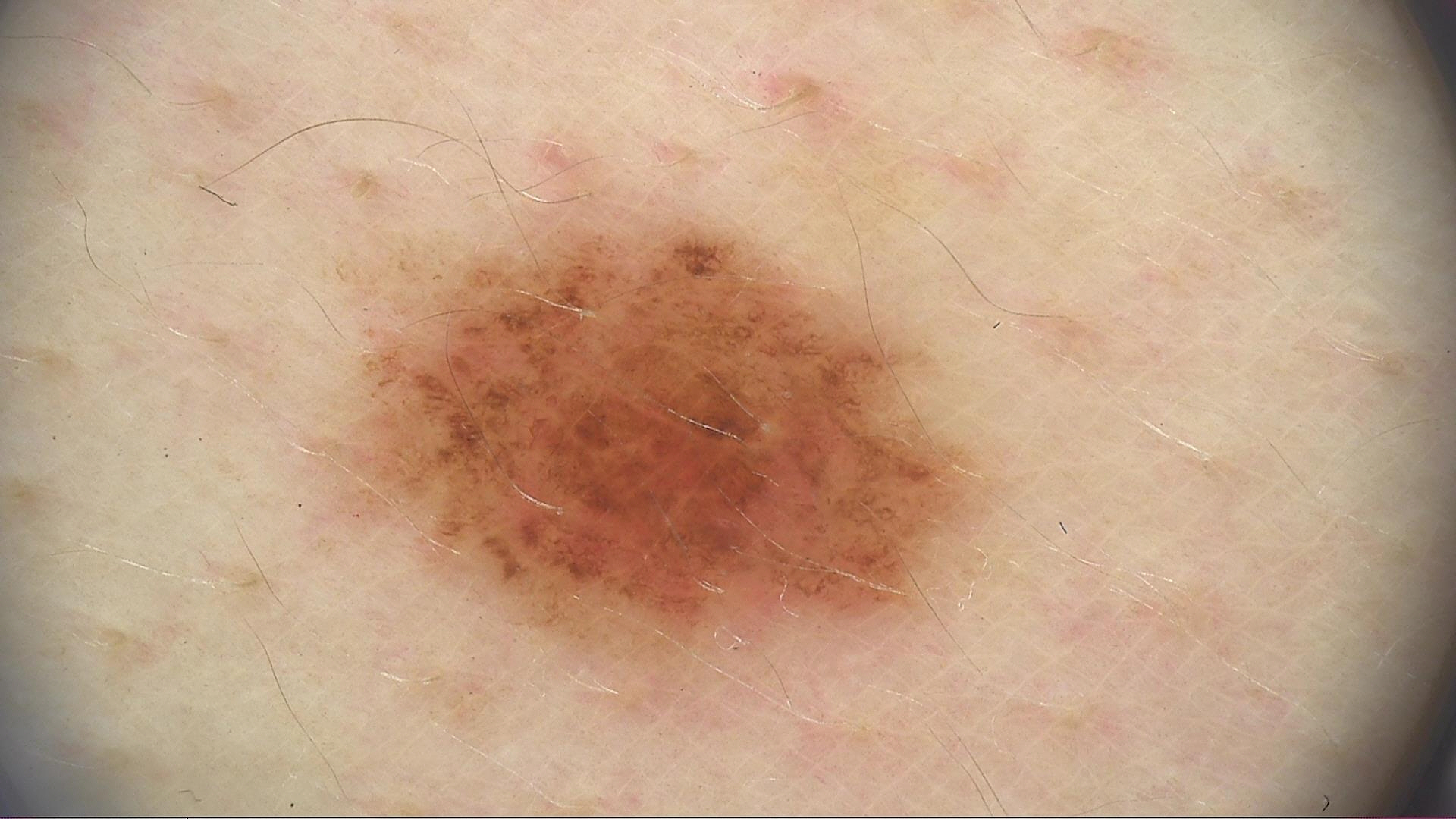Case: A dermoscopic photograph of a skin lesion. Impression: Labeled as a dysplastic junctional nevus.